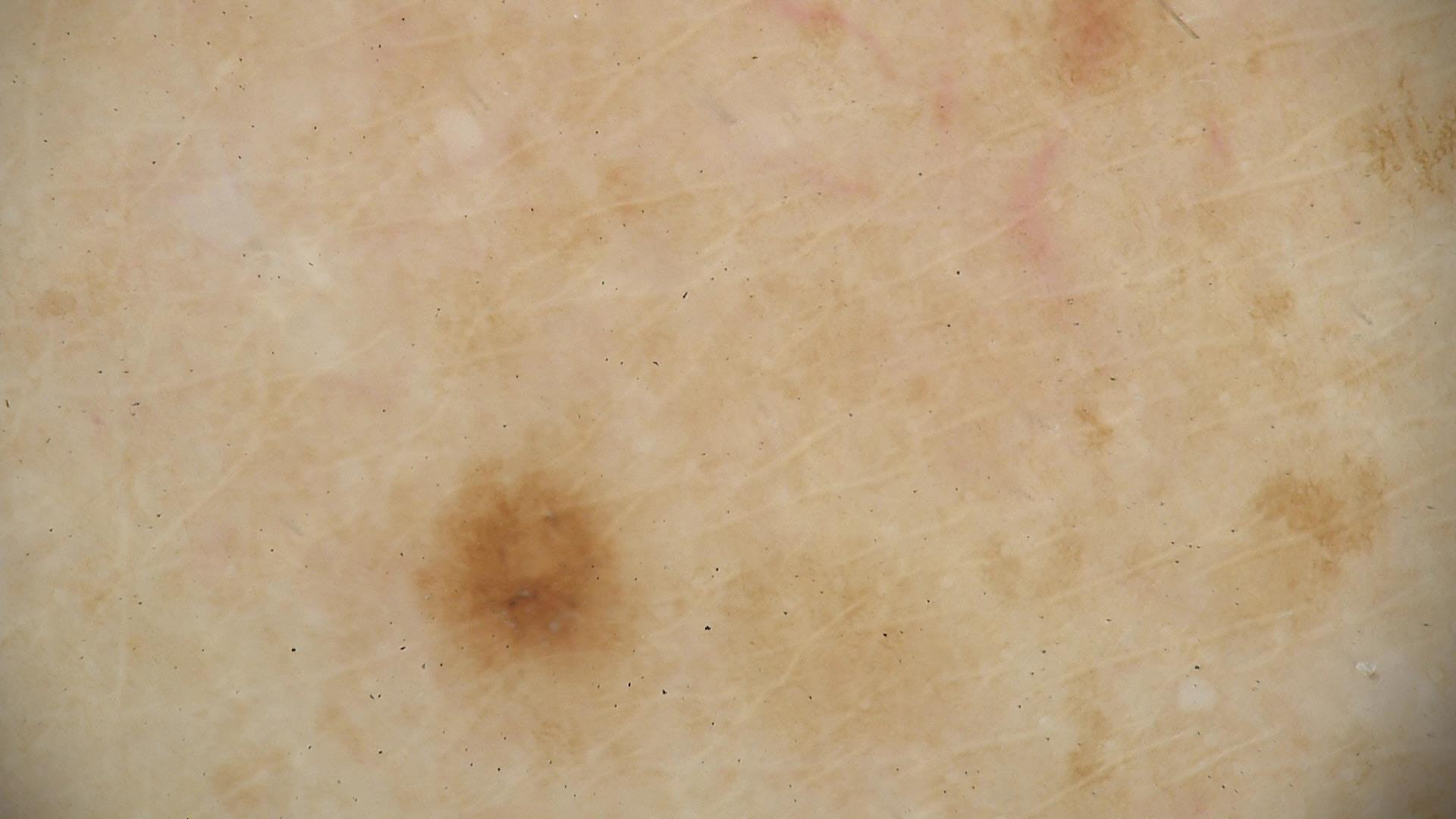class: dysplastic junctional nevus (expert consensus).